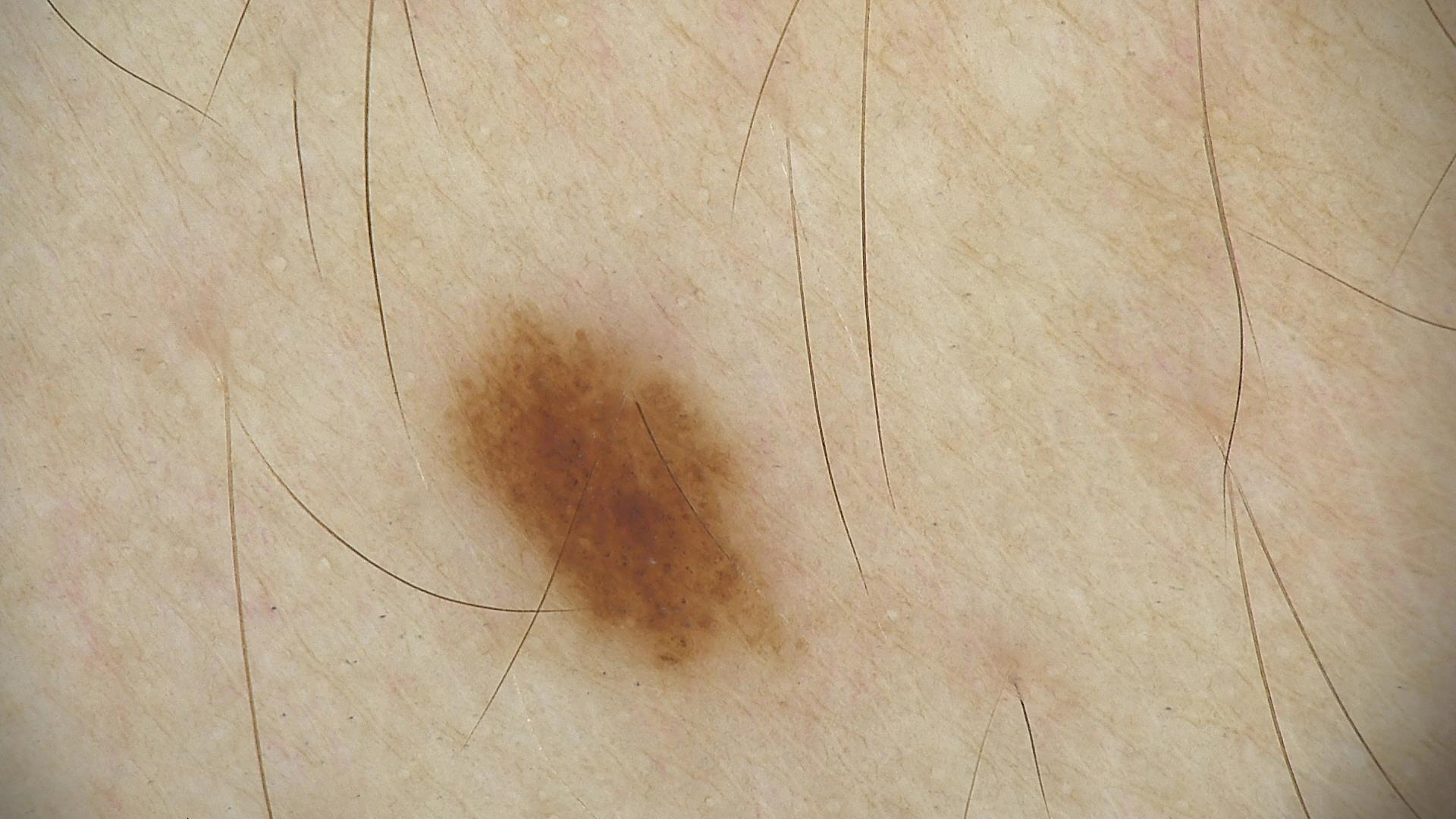Case:
- image type: dermoscopy
- diagnosis: dysplastic junctional nevus (expert consensus)